The photo was captured at an angle · the lesion involves the leg · female patient, age 60–69 — 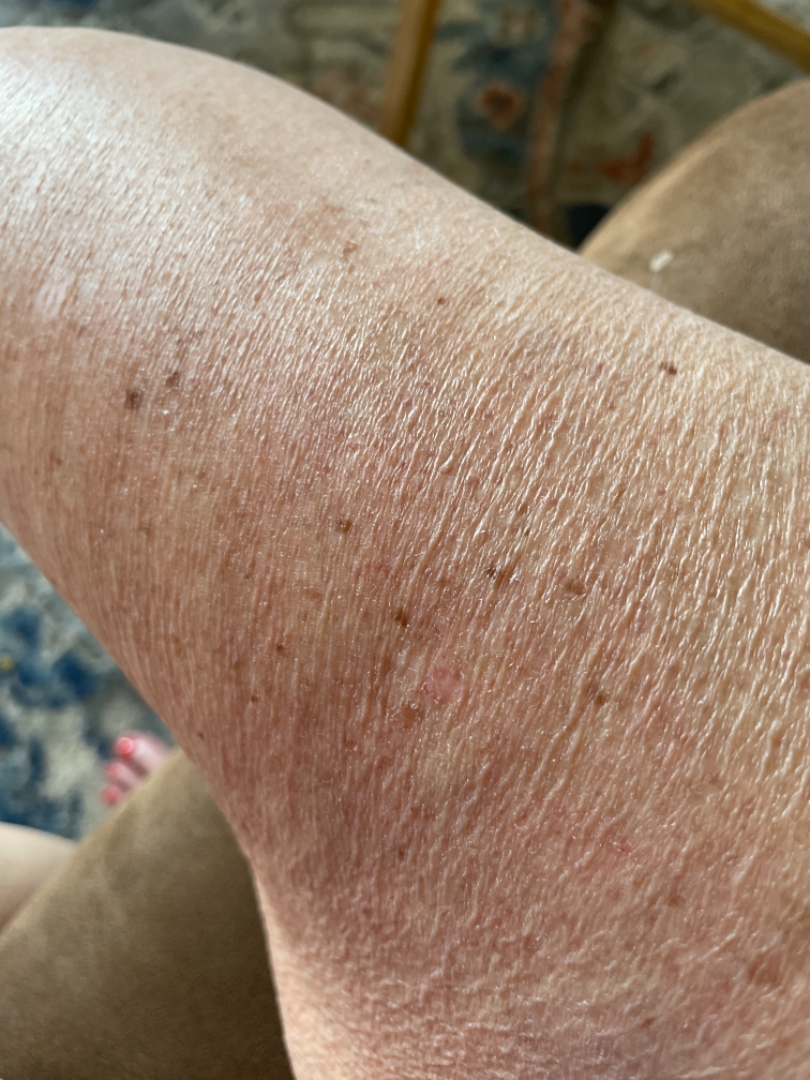The skin condition could not be confidently assessed from this image.
The patient reported no relevant symptoms from the lesion.
The patient considered this skin that appeared healthy to them.
The lesion is described as flat.
The condition has been present for about one day.